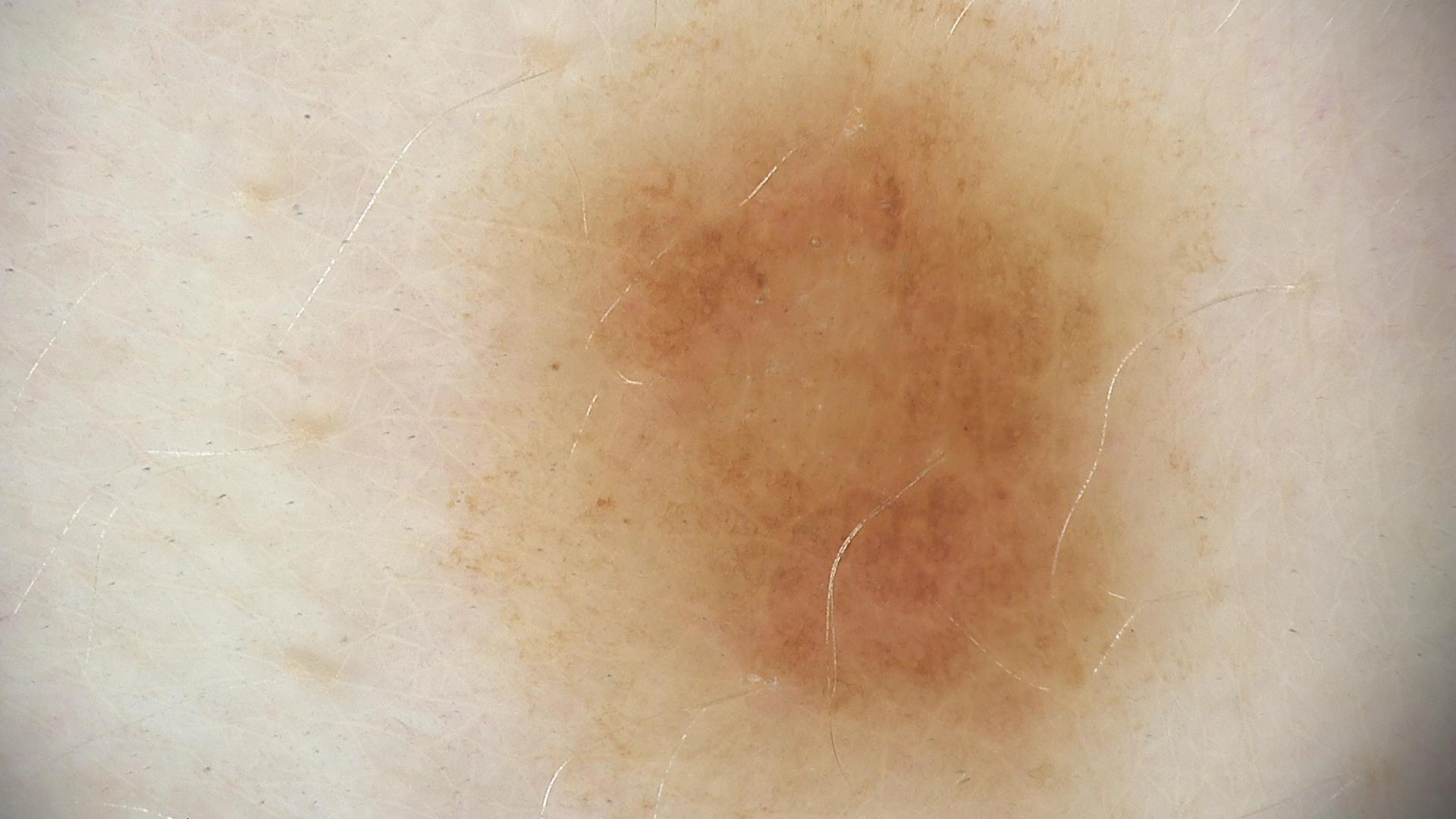Summary:
A skin lesion imaged with a dermatoscope.
Conclusion:
The diagnosis was a benign lesion — a dysplastic junctional nevus.